Dermoscopy of a skin lesion: 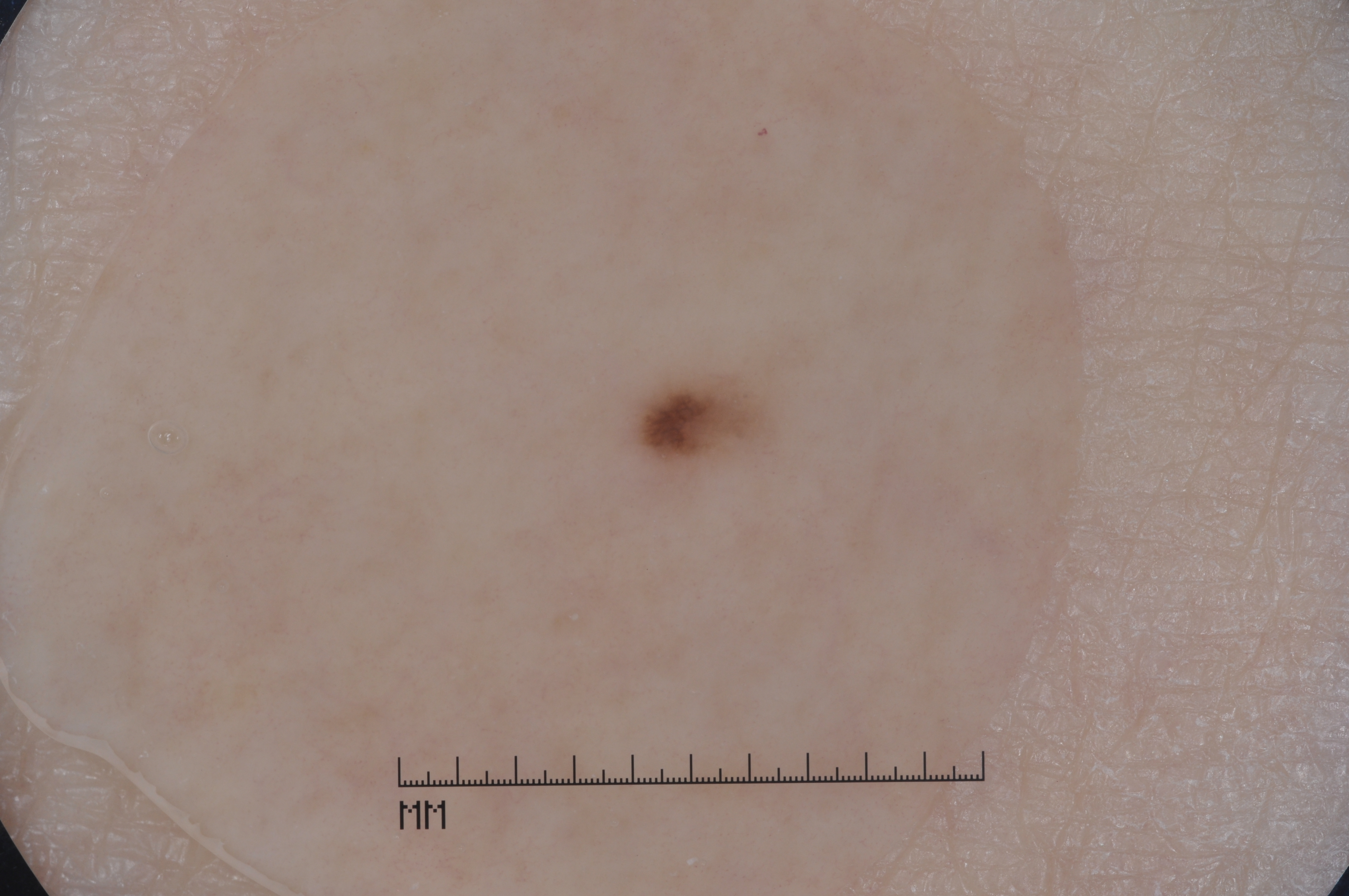Dermoscopy demonstrates pigment network and milia-like cysts. In (x1, y1, x2, y2) order, lesion location: bbox=[617, 359, 780, 496]. The lesion was assessed as a melanocytic nevus.